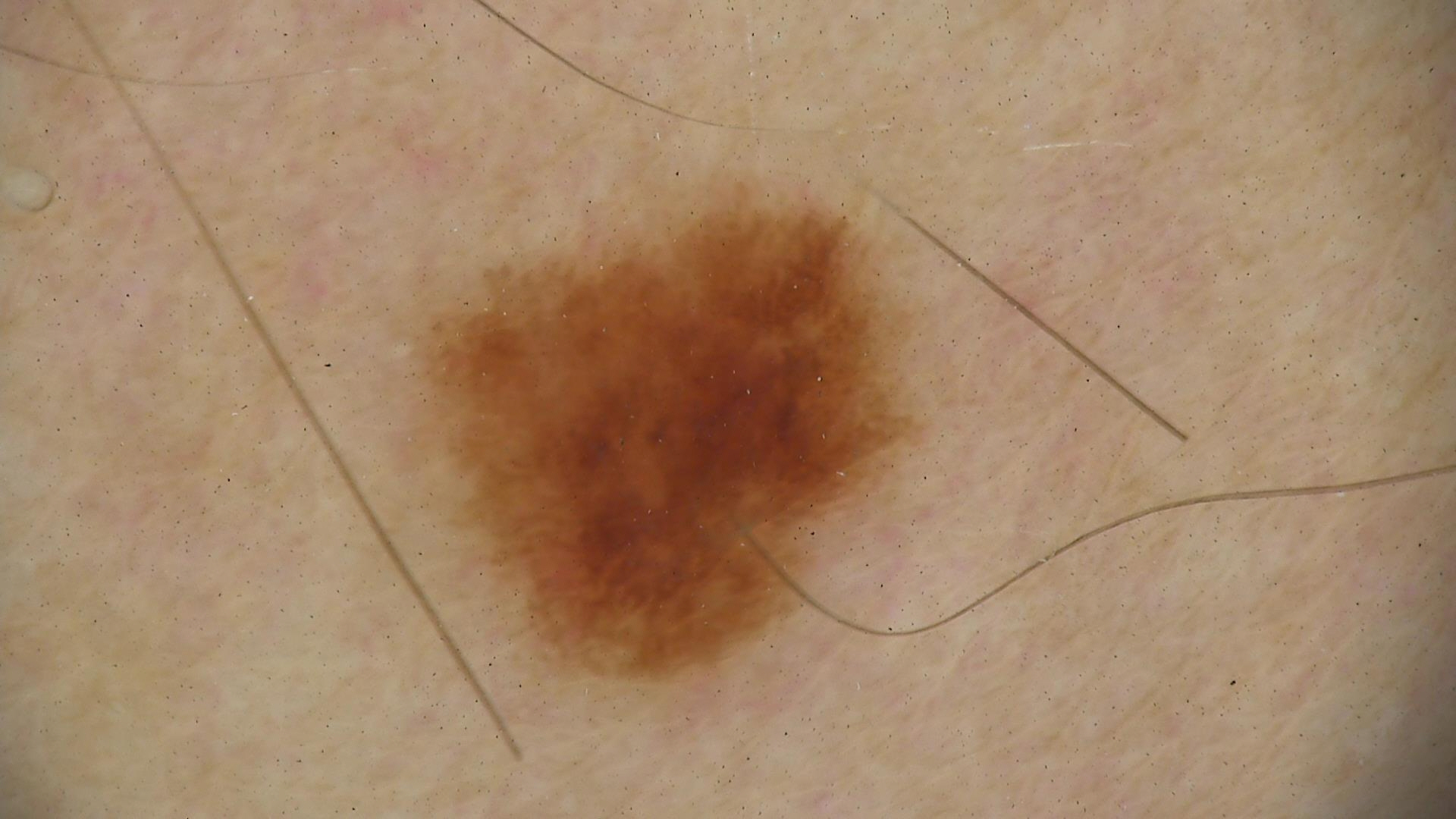<lesion>
  <image>dermoscopy</image>
  <diagnosis>
    <name>dysplastic junctional nevus</name>
    <code>jd</code>
    <malignancy>benign</malignancy>
    <super_class>melanocytic</super_class>
    <confirmation>expert consensus</confirmation>
  </diagnosis>
</lesion>